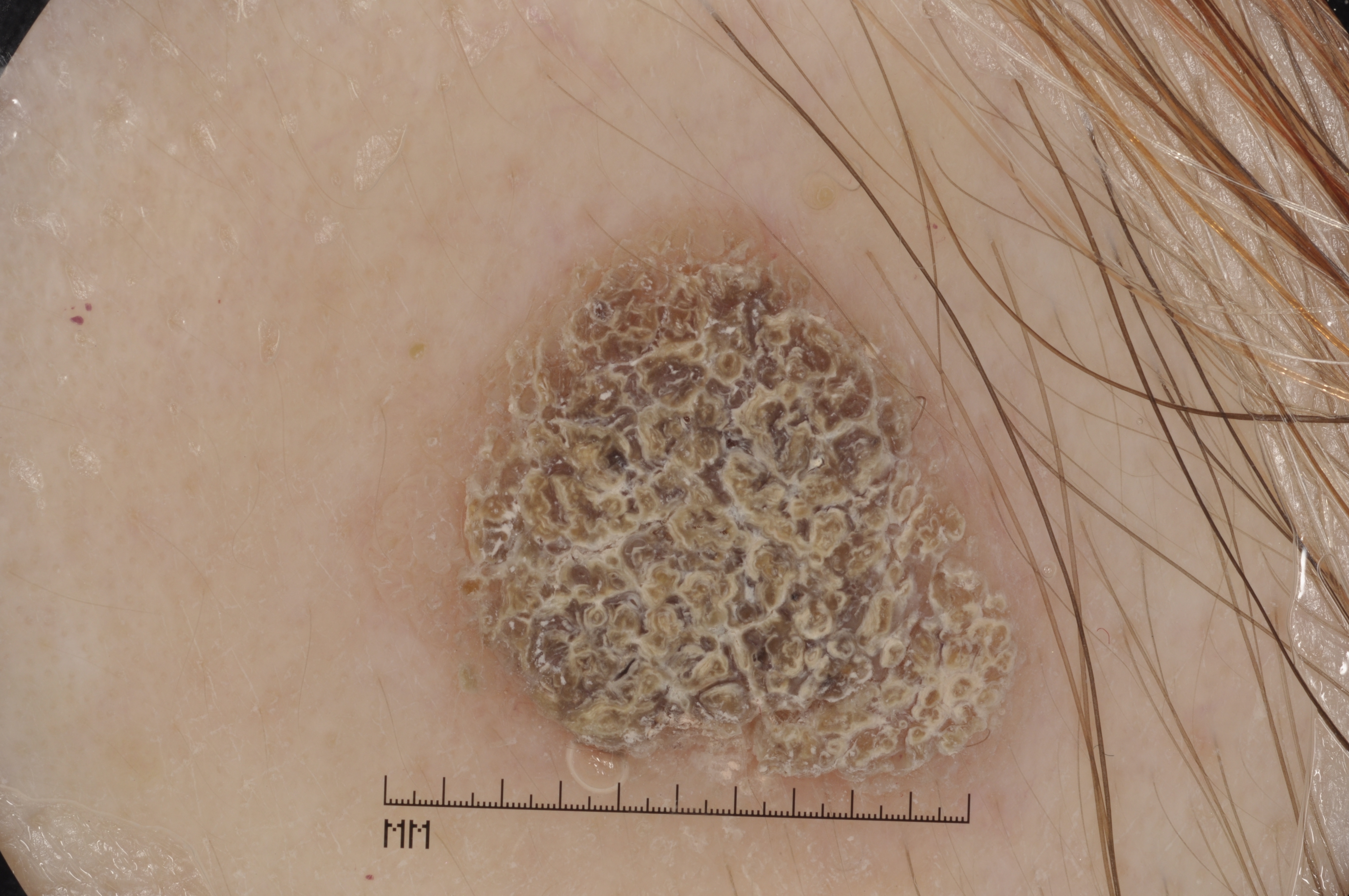Findings: The subject is a female aged approximately 60. A dermatoscopic image of a skin lesion. The lesion takes up a moderate portion of the field. As (left, top, right, bottom), the visible lesion spans bbox=[369, 203, 1075, 826]. The dermoscopic pattern shows no negative network, pigment network, streaks, or milia-like cysts. Conclusion: Diagnosed as a seborrheic keratosis.